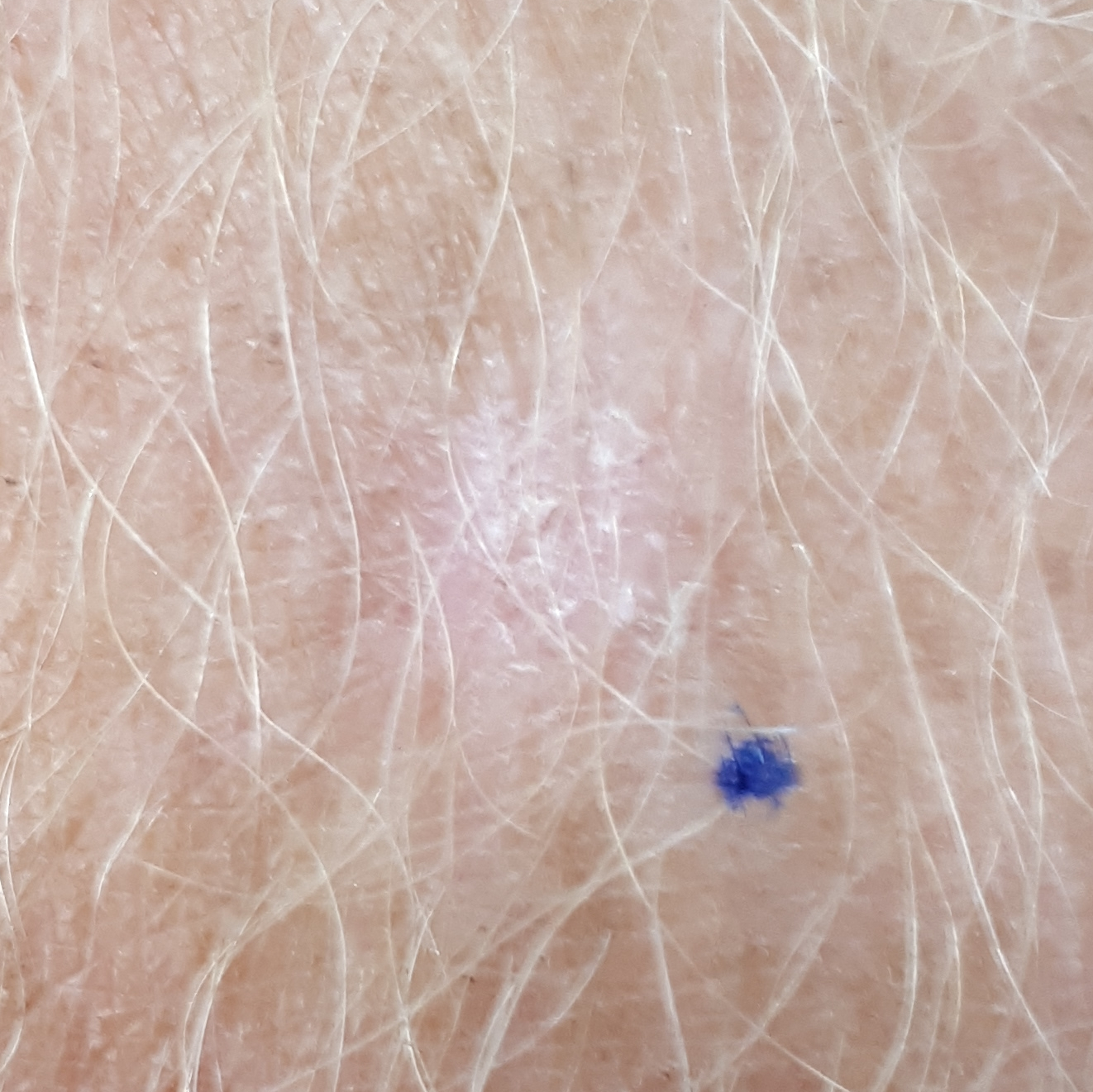Patient and lesion: By history, pesticide exposure and alcohol use. A male patient 39 years of age. The patient is FST II. The lesion is located on a forearm. The lesion is roughly 10 by 10 mm. Pathology: On biopsy, the diagnosis was a lesion of indeterminate malignant potential — an actinic keratosis.